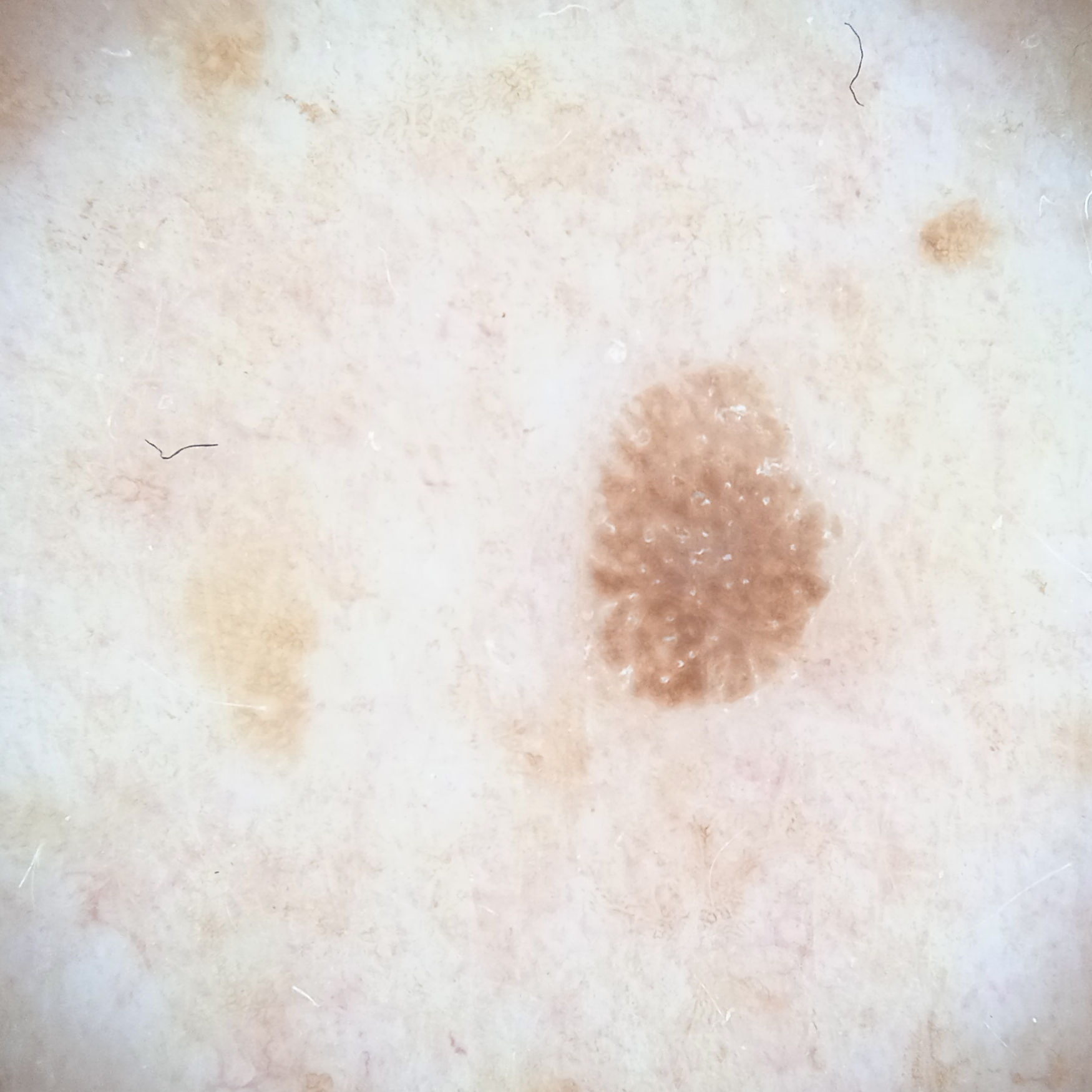<case>
  <mole_burden>few melanocytic nevi overall</mole_burden>
  <sun_reaction>skin reddens with sun exposure</sun_reaction>
  <referral>research study (no referral diagnosis)</referral>
  <patient>
    <age>62</age>
    <sex>male</sex>
  </patient>
  <image>dermoscopic image</image>
  <lesion_location>the back</lesion_location>
  <lesion_size>
    <diameter_mm>4.3</diameter_mm>
  </lesion_size>
  <diagnosis>
    <name>seborrheic keratosis</name>
    <malignancy>benign</malignancy>
  </diagnosis>
</case>